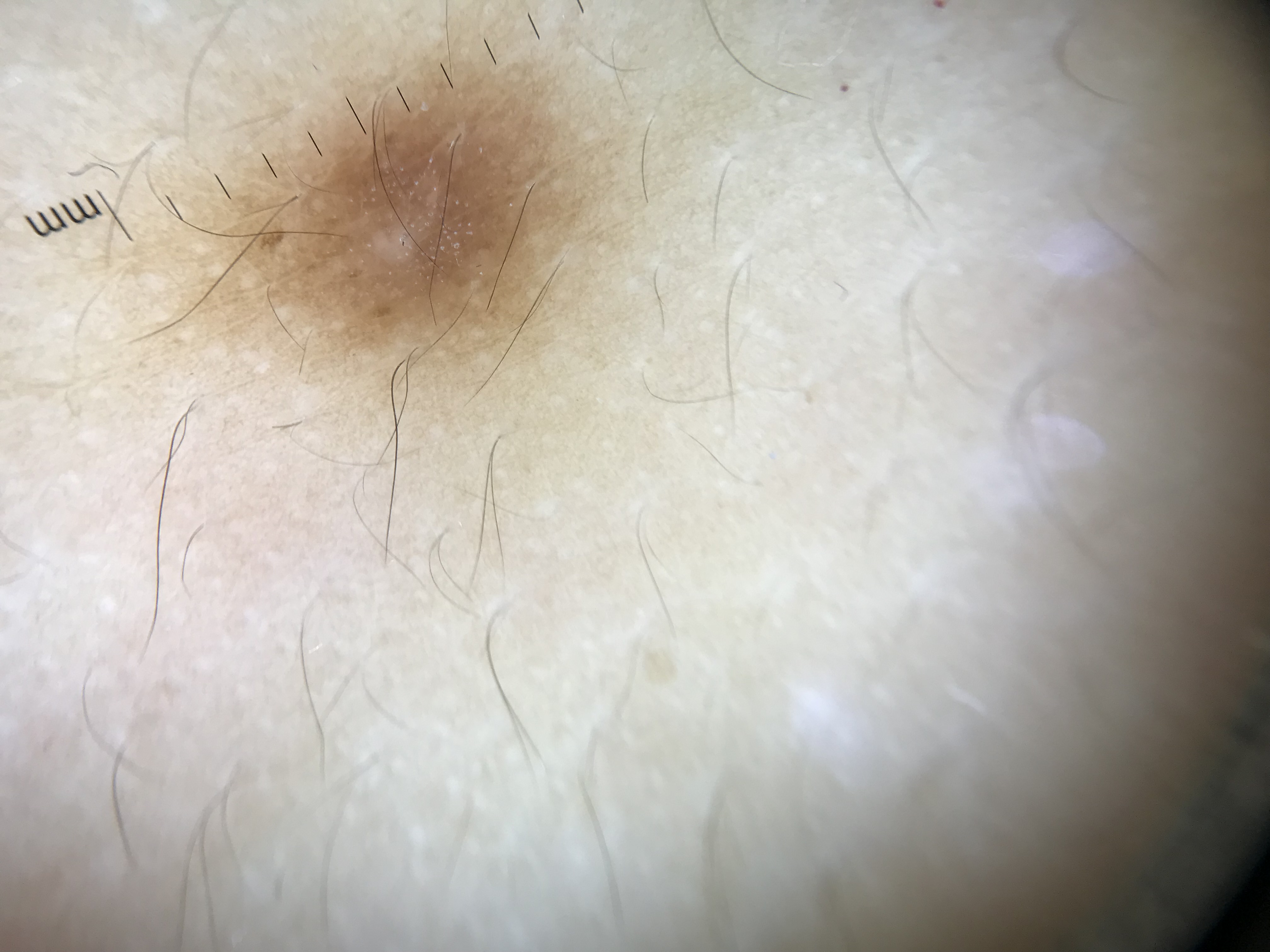| feature | finding |
|---|---|
| diagnosis | dermatofibroma (expert consensus) |